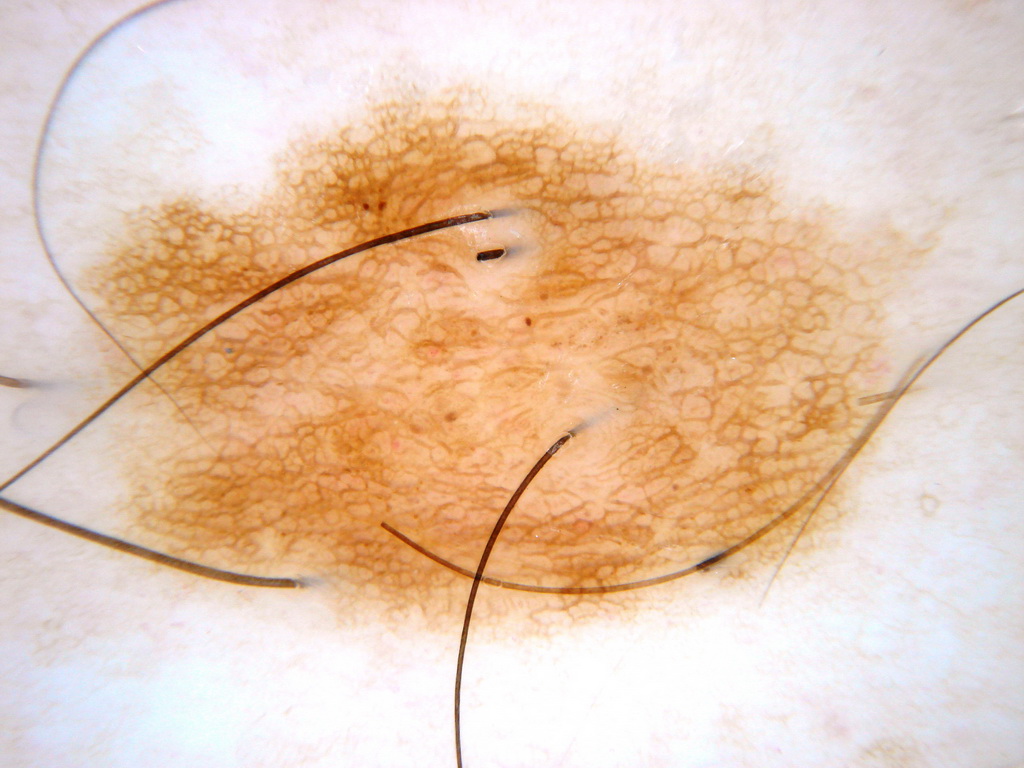A dermoscopic view of a skin lesion. A female subject, aged approximately 25. Dermoscopy demonstrates globules and pigment network, with no streaks, milia-like cysts, or negative network. The visible lesion spans [75, 56, 937, 647]. The clinical diagnosis was a melanocytic nevus.